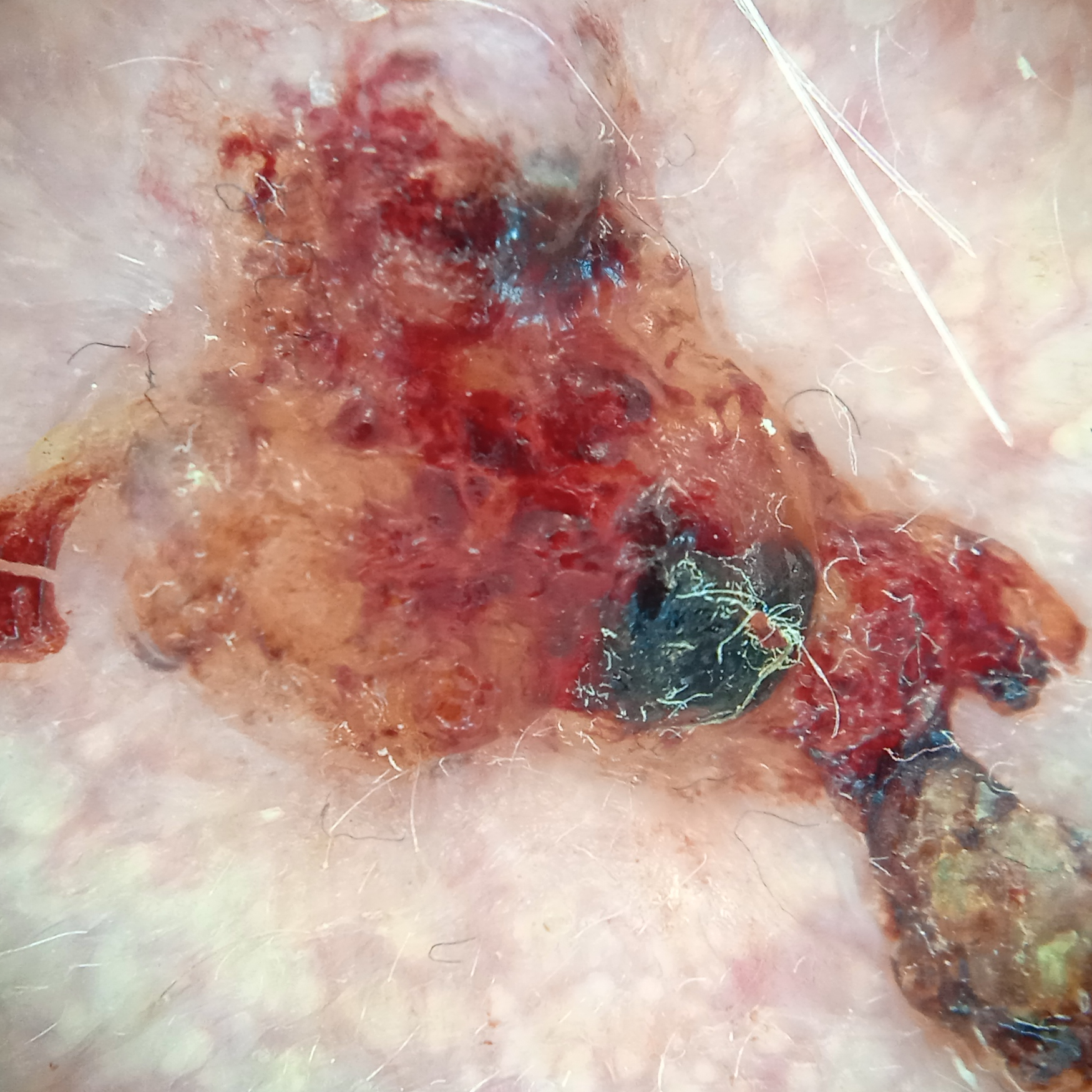Case:
– image type: dermatoscopic image
– referral: clinical suspicion of basal cell carcinoma
– subject: male, age 89
– anatomic site: the face
– size: 14.9 mm
– diagnosis: basal cell carcinoma (biopsy-proven)